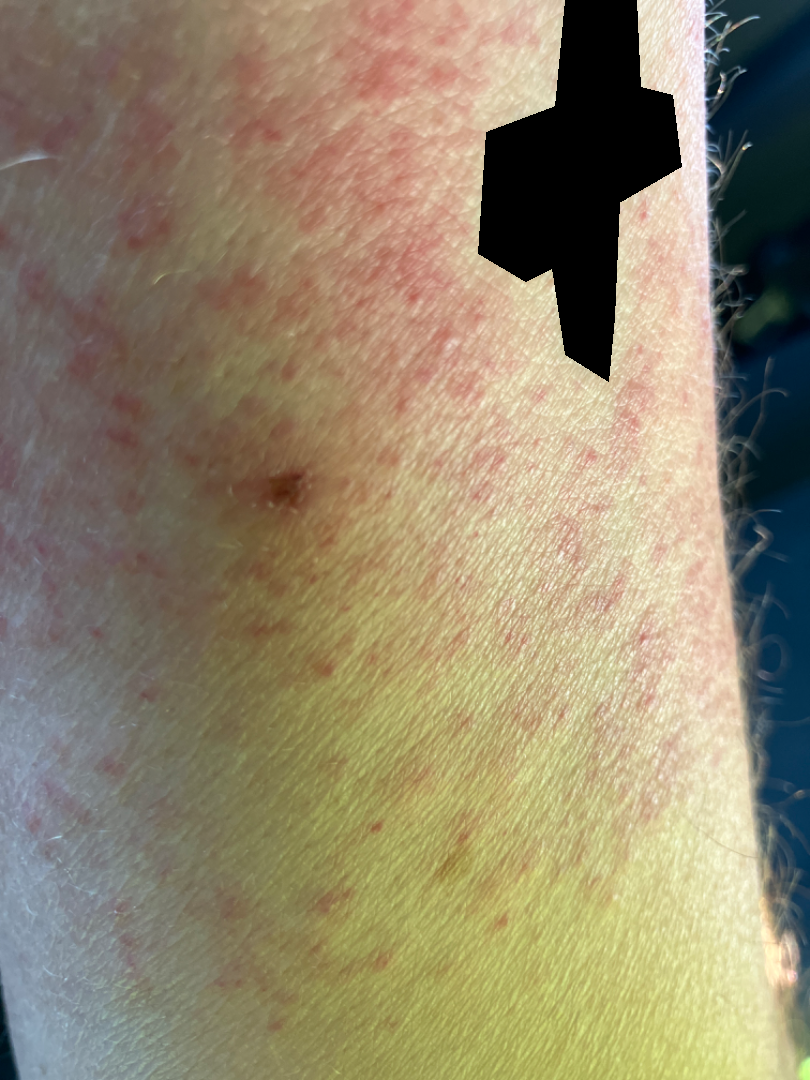Notes:
– assessment: not assessable
– contributor: male, age 50–59
– view: at an angle